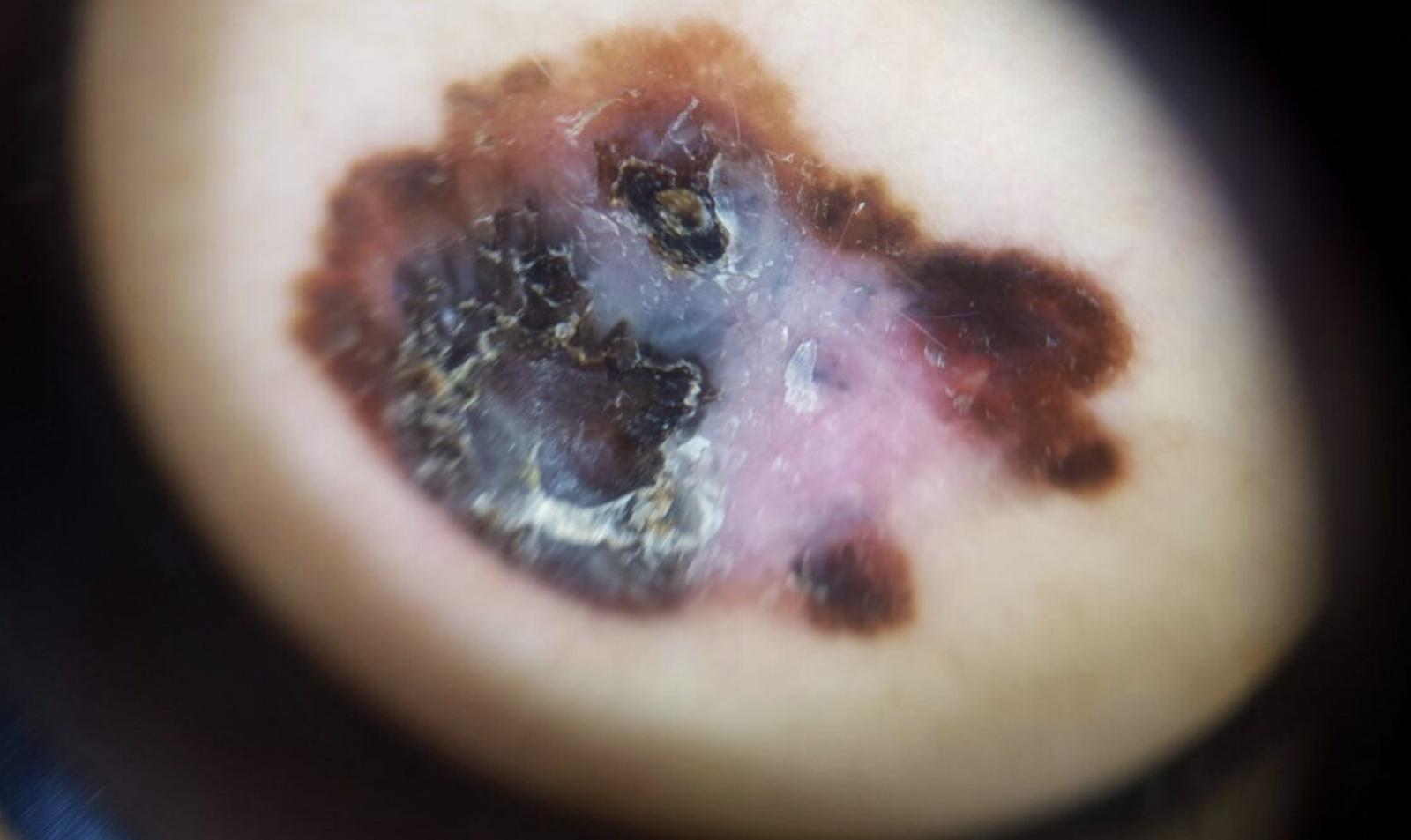Findings: The chart records a first-degree relative with melanoma and a previous melanoma. Contact-polarized dermoscopy of a skin lesion. A male patient approximately 50 years of age. Conclusion: Histopathological examination showed a melanoma.